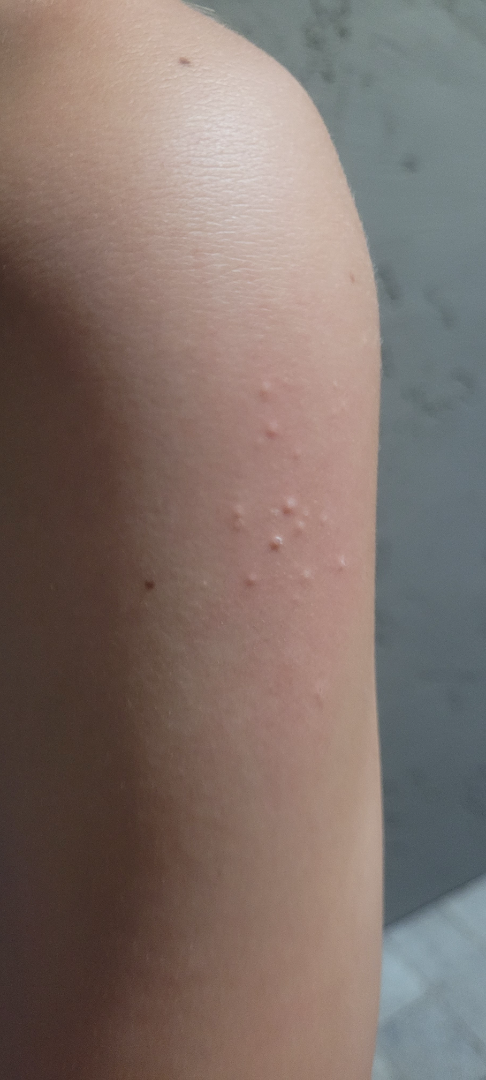The reviewing dermatologist was unable to assign a differential diagnosis from the image.
The patient is a female aged 18–29.
Located on the arm.
The photo was captured at an angle.